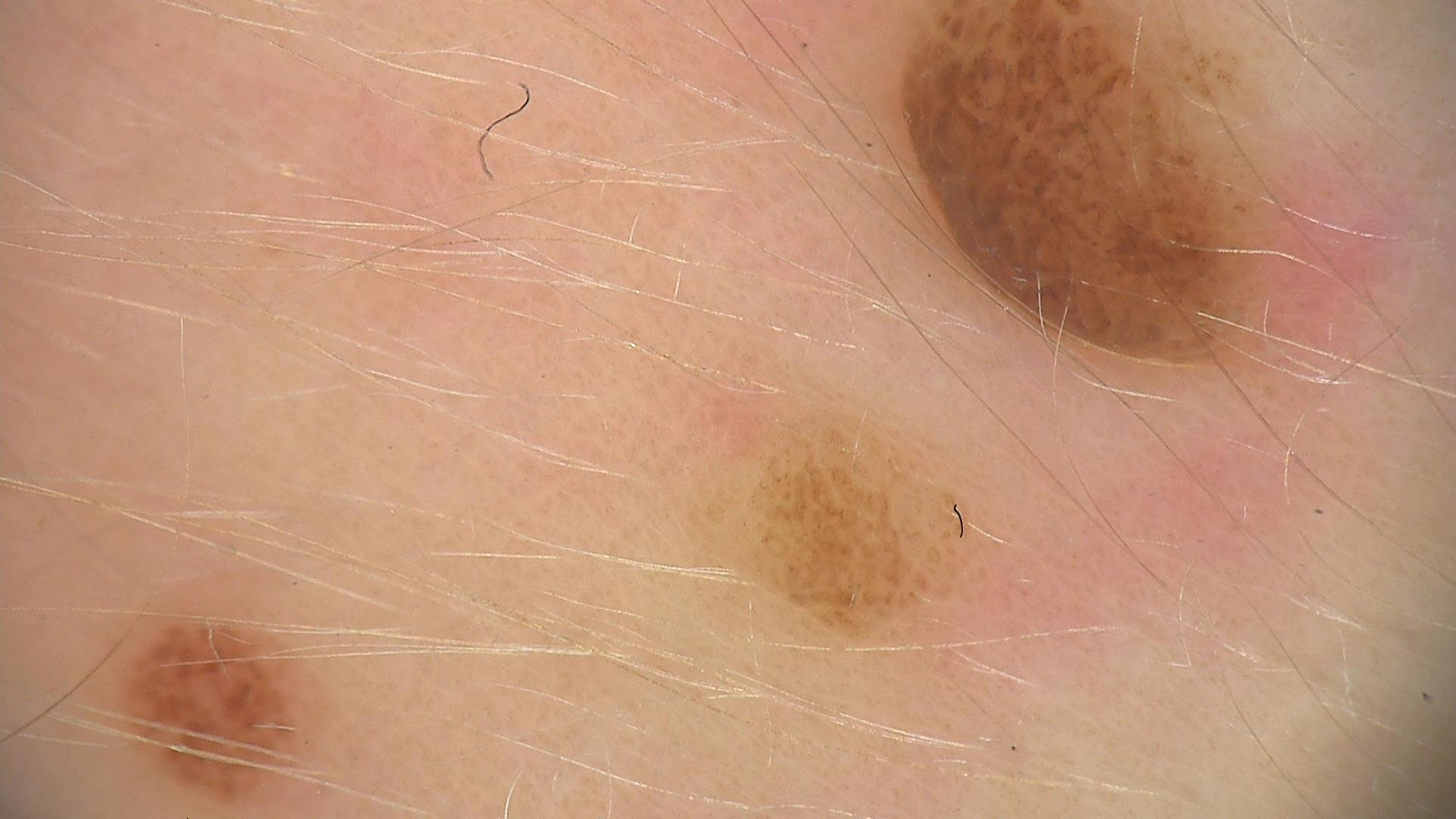A skin lesion imaged with a dermatoscope.
Consistent with a banal lesion — a compound nevus.